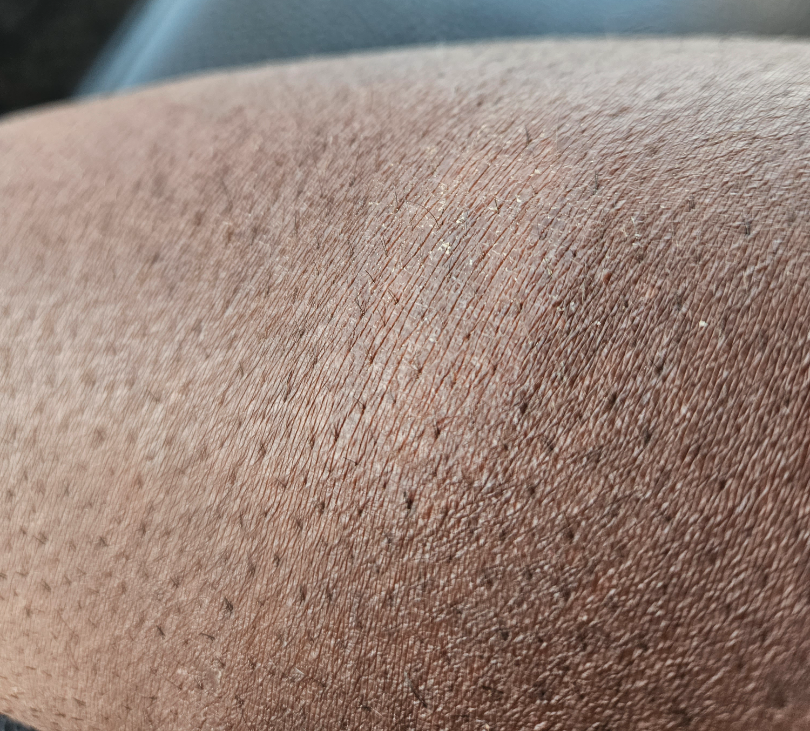Findings:
The reviewer was unable to grade this case for skin condition.
Background:
The affected area is the arm and head or neck. Close-up view. Male patient, age 40–49.